Close-up view. Located on the back of the torso: 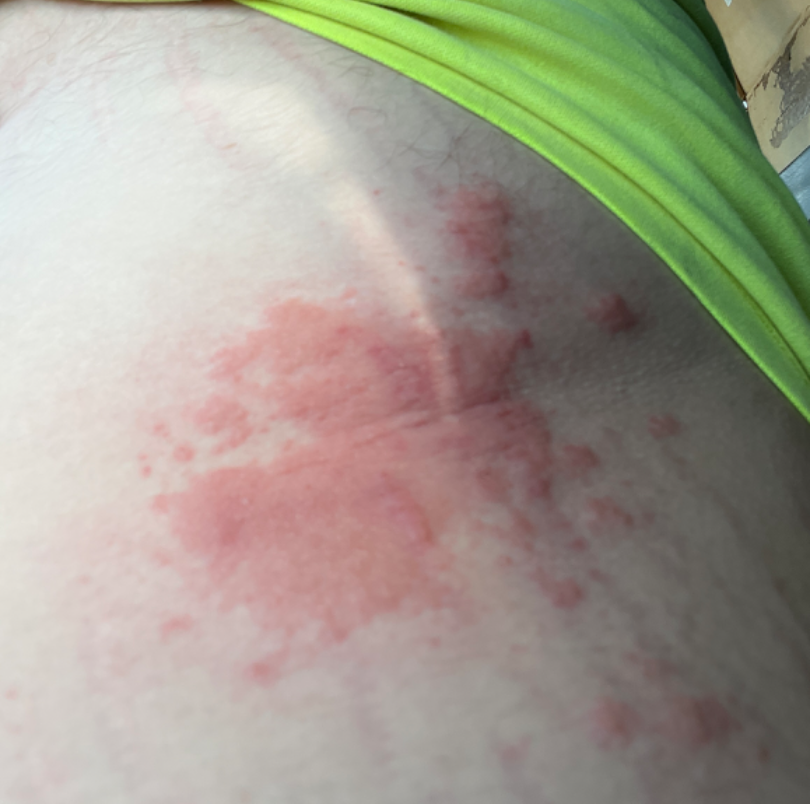Q: Could the case be diagnosed?
A: indeterminate
Q: When did this start?
A: less than one week